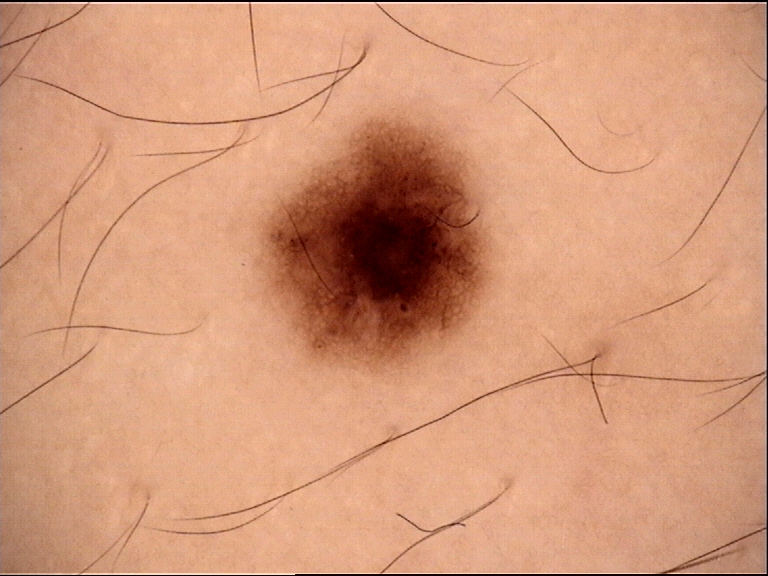Labeled as a benign lesion — a dysplastic junctional nevus.